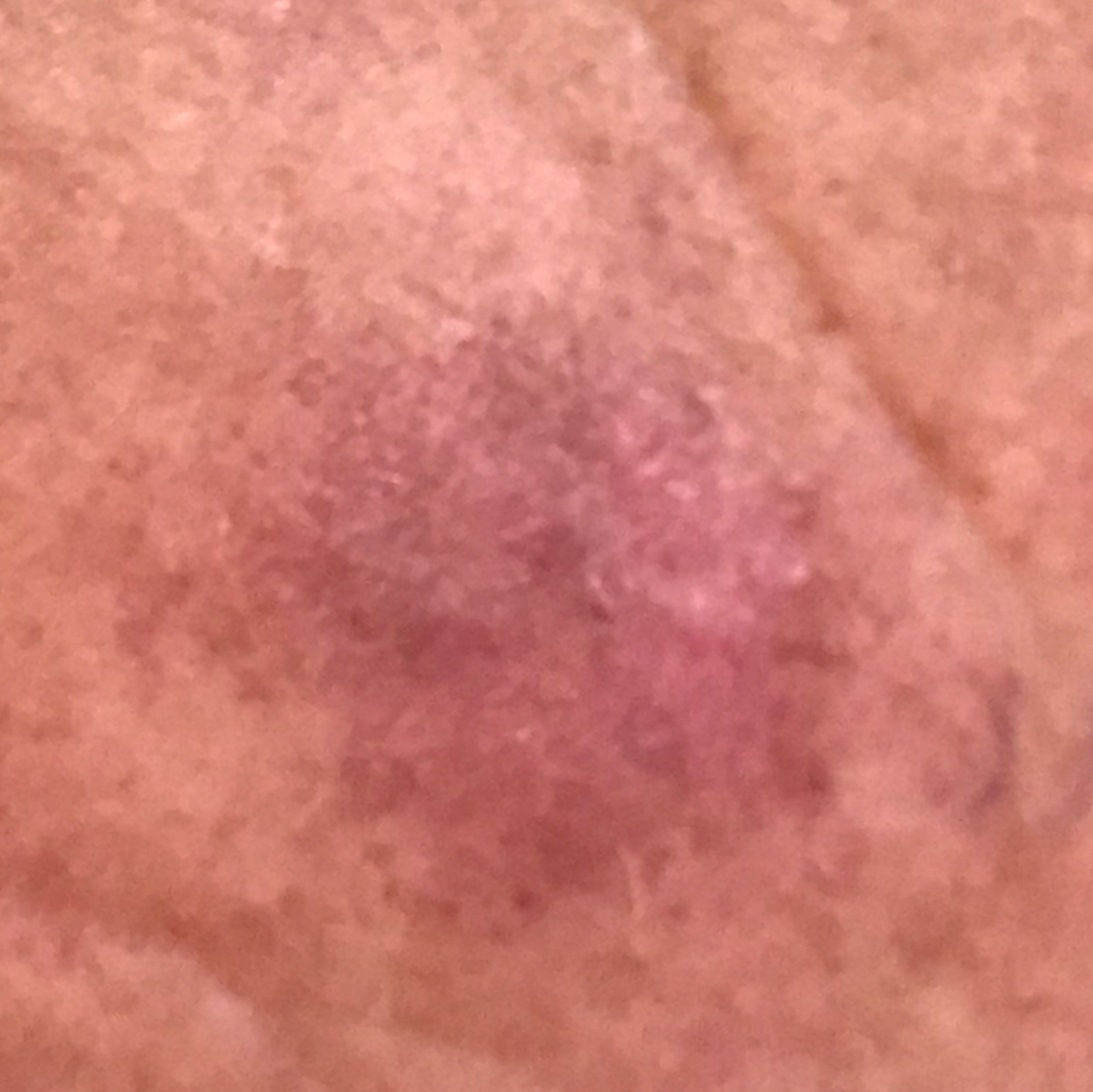Impression:
Clinically diagnosed as an actinic keratosis.